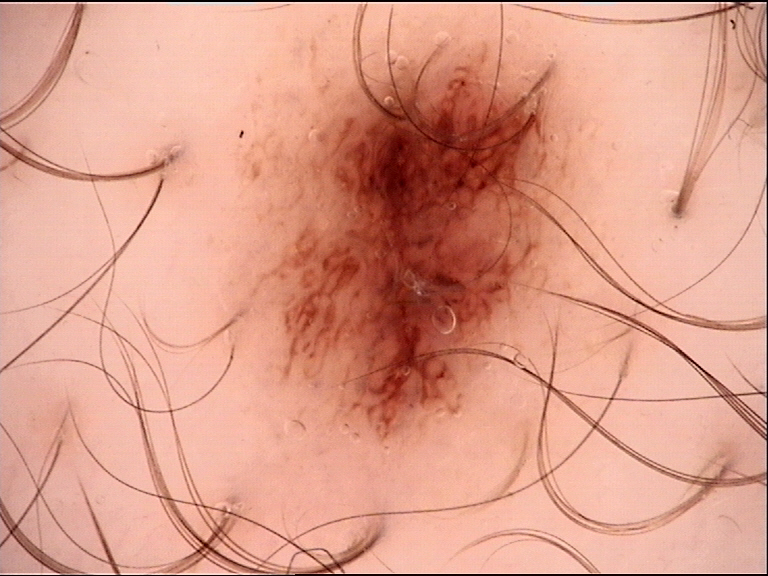A skin lesion imaged with a dermatoscope. Consistent with a benign lesion — a dysplastic junctional nevus.